The lesion involves the head or neck, palm, leg and arm. A close-up photograph. Female patient, age 30–39.
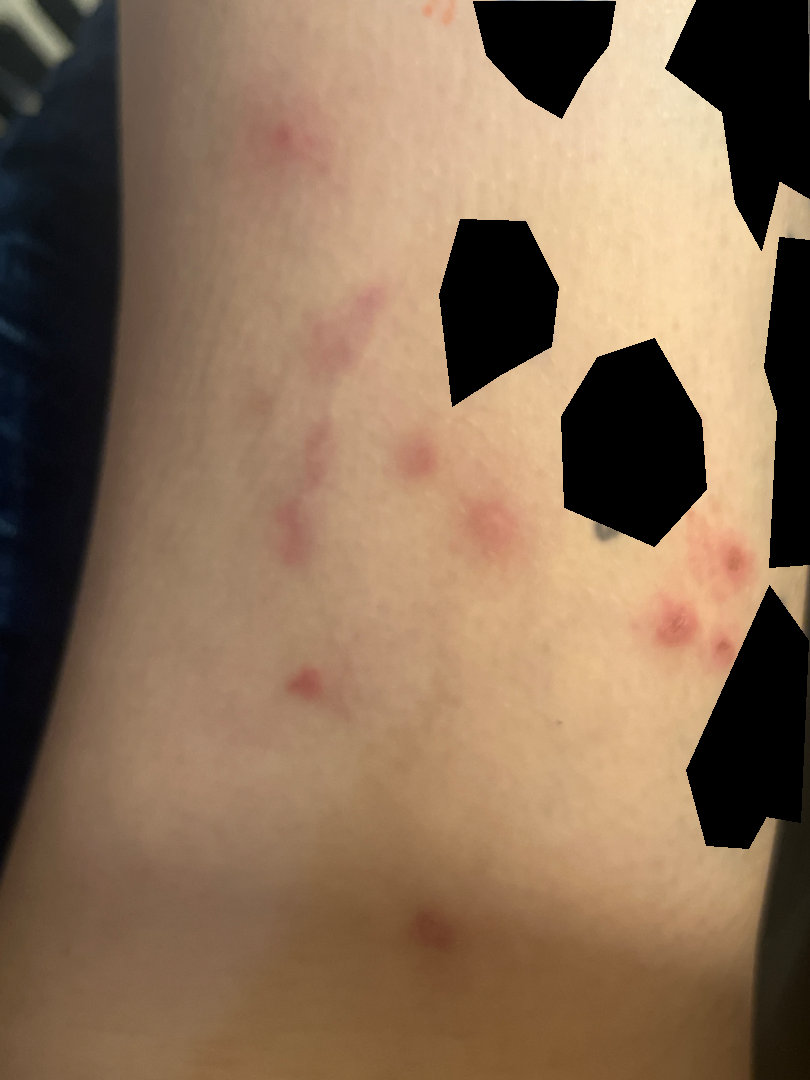| key | value |
|---|---|
| reported symptoms | itching, burning, darkening and pain |
| systemic symptoms | shortness of breath, joint pain and chills |
| onset | since childhood |
| patient describes the issue as | a rash |
| differential | favoring Prurigo nodularis; also raised was Folliculitis |